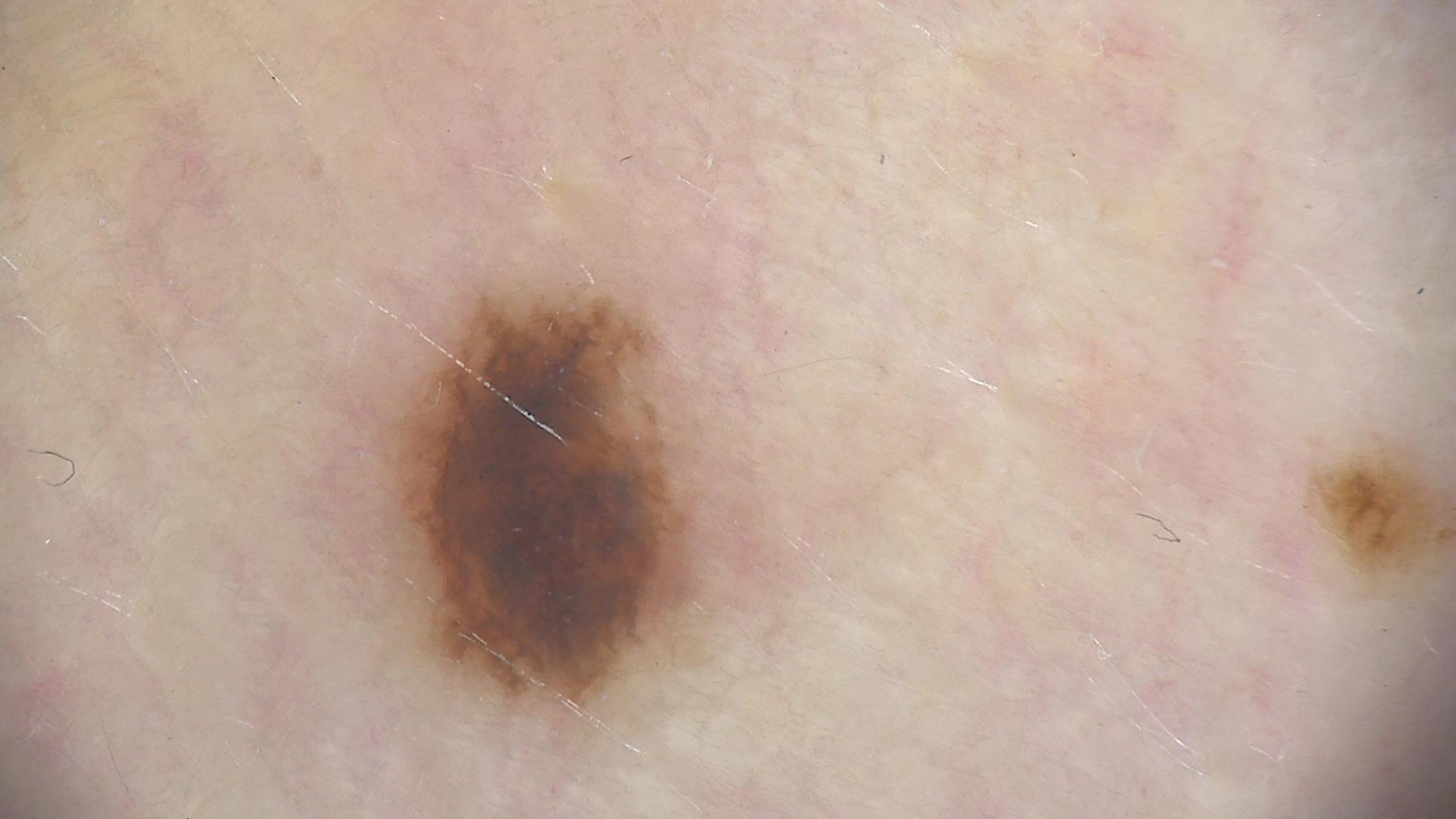The diagnosis was a dysplastic junctional nevus.